Collected as part of a research study, without a referral diagnosis. A female patient 81 years of age. Dermoscopy of a skin lesion. The patient describes having a moderate number of moles:
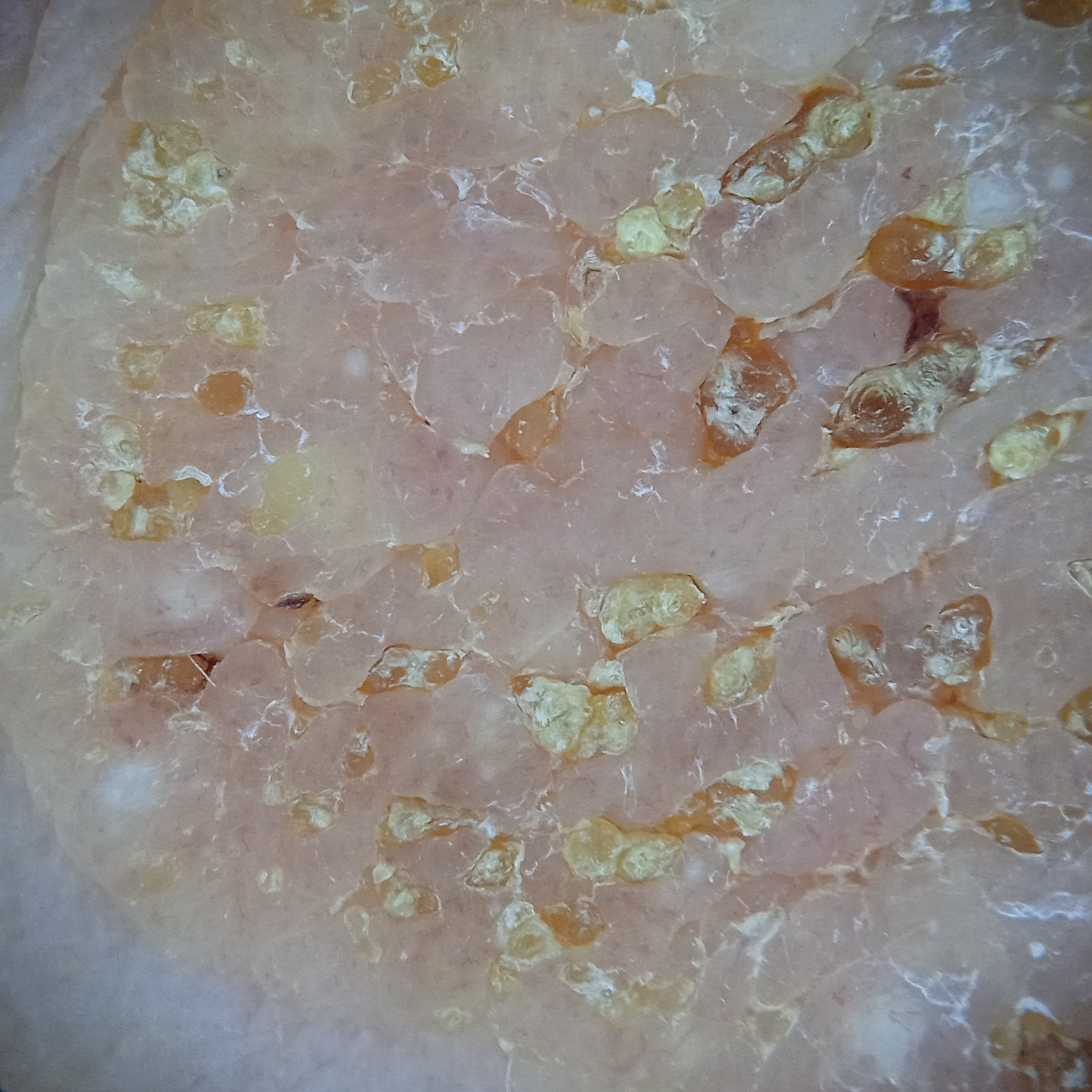The lesion is about 31 mm across.
Dermatologist review favored a seborrheic keratosis.